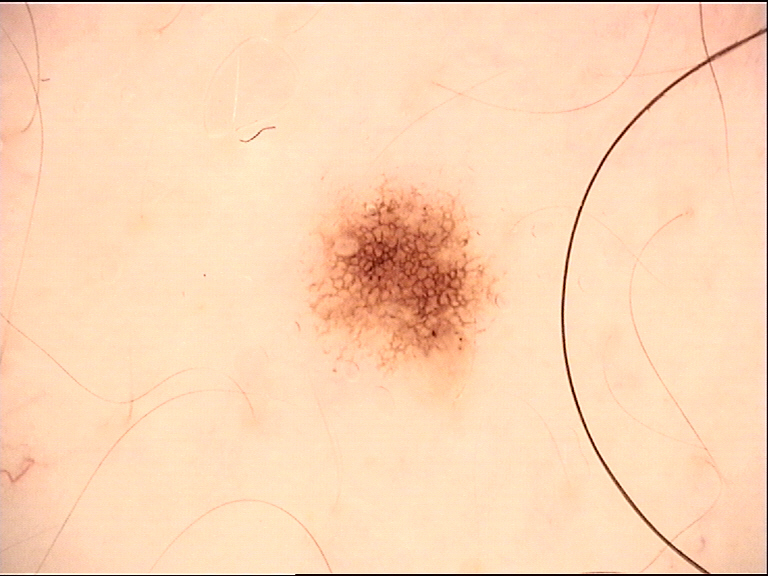The diagnosis was a dysplastic junctional nevus.